Close-up view:
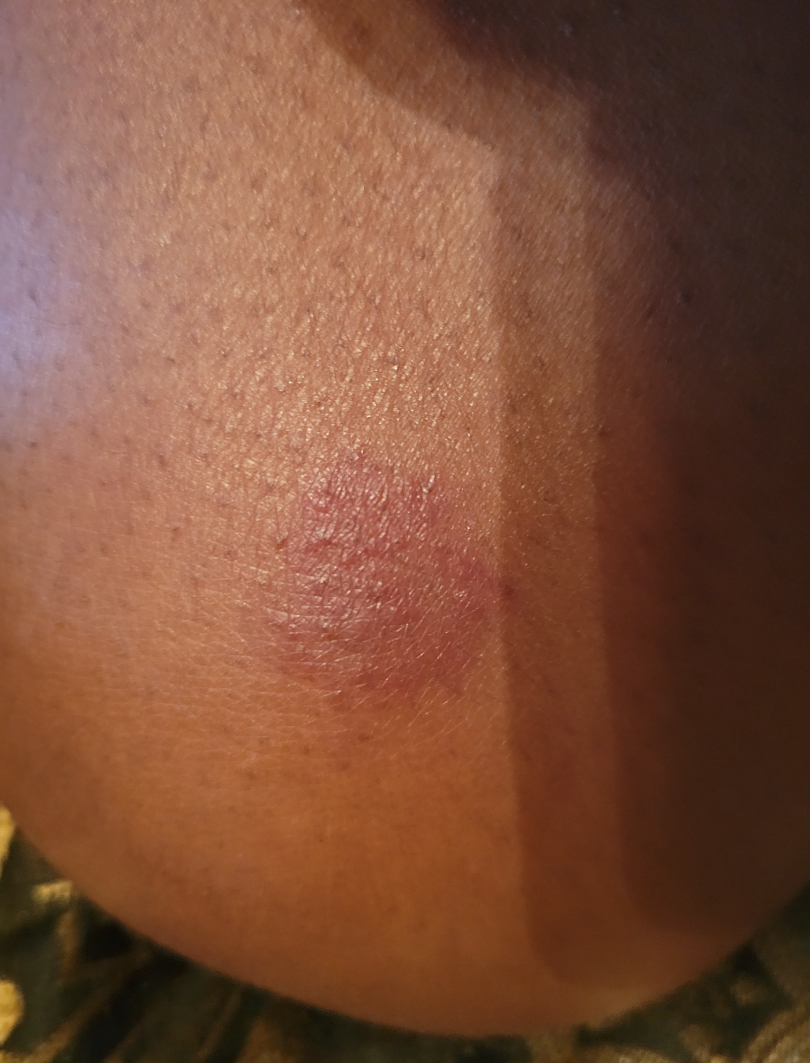The reviewing dermatologist was unable to assign a differential diagnosis from the image.